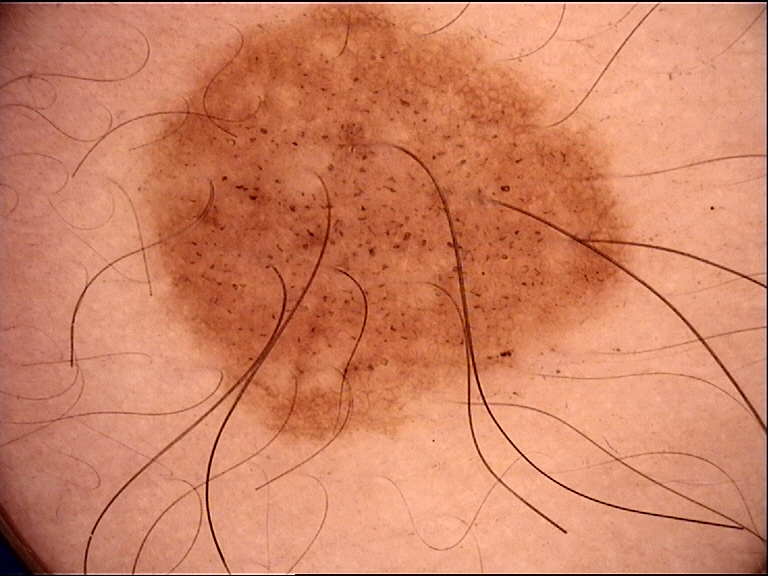Q: How is the lesion classified?
A: banal
Q: What is this lesion?
A: junctional nevus (expert consensus)